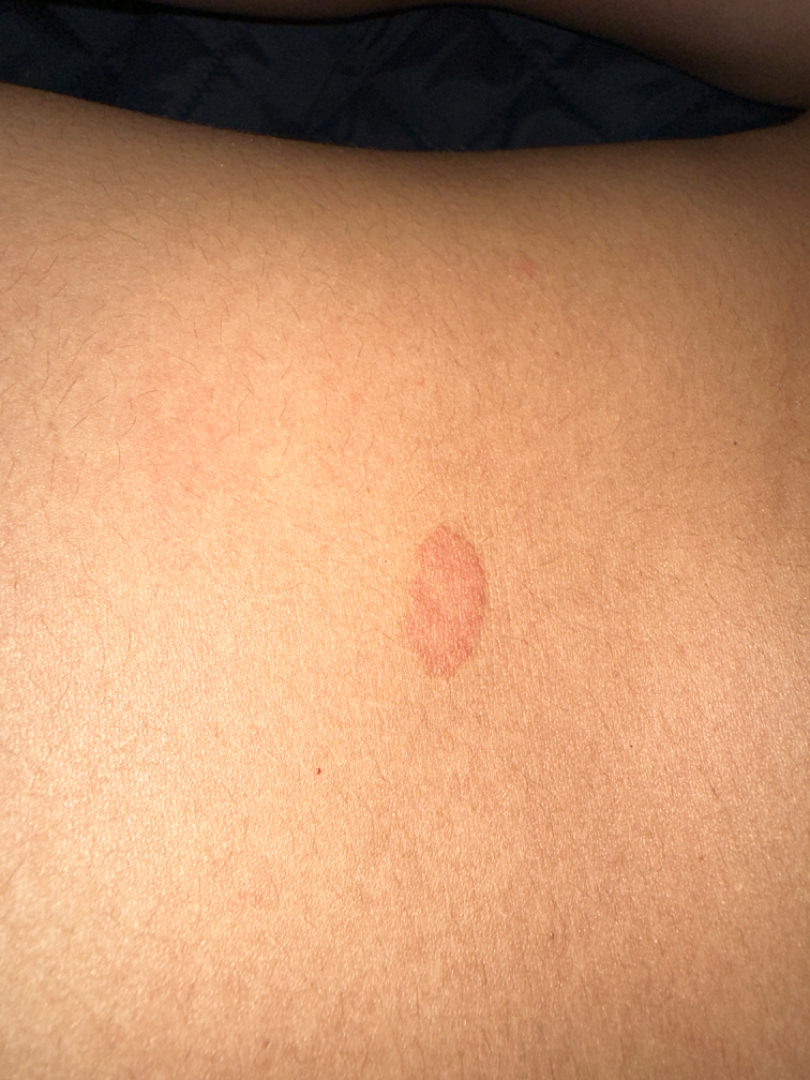Review:
The case was indeterminate on photographic review.
Patient information:
A close-up photograph.